A clinical photograph of a skin lesion; a patient aged 55 — 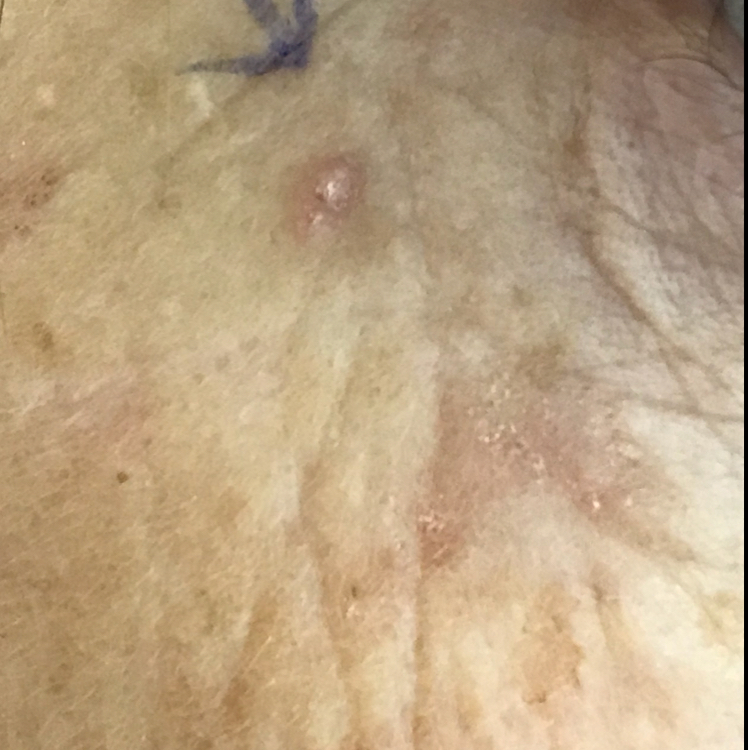Summary:
The patient describes that the lesion has grown and itches, but is not elevated and has not bled.
Conclusion:
Consistent with an actinic keratosis.